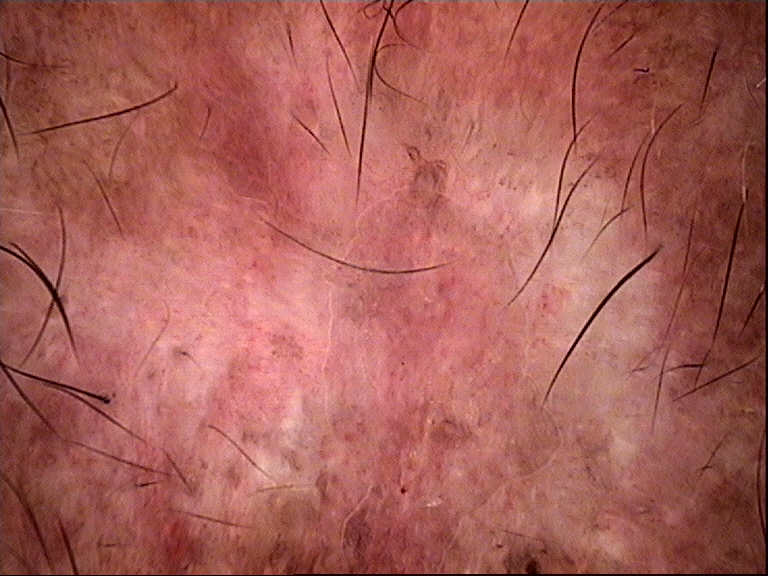Summary: A dermoscopy image of a single skin lesion. This is a keratinocytic lesion. Conclusion: The biopsy diagnosis was a basal cell carcinoma.